Close-up view. Skin tone: Fitzpatrick skin type II.
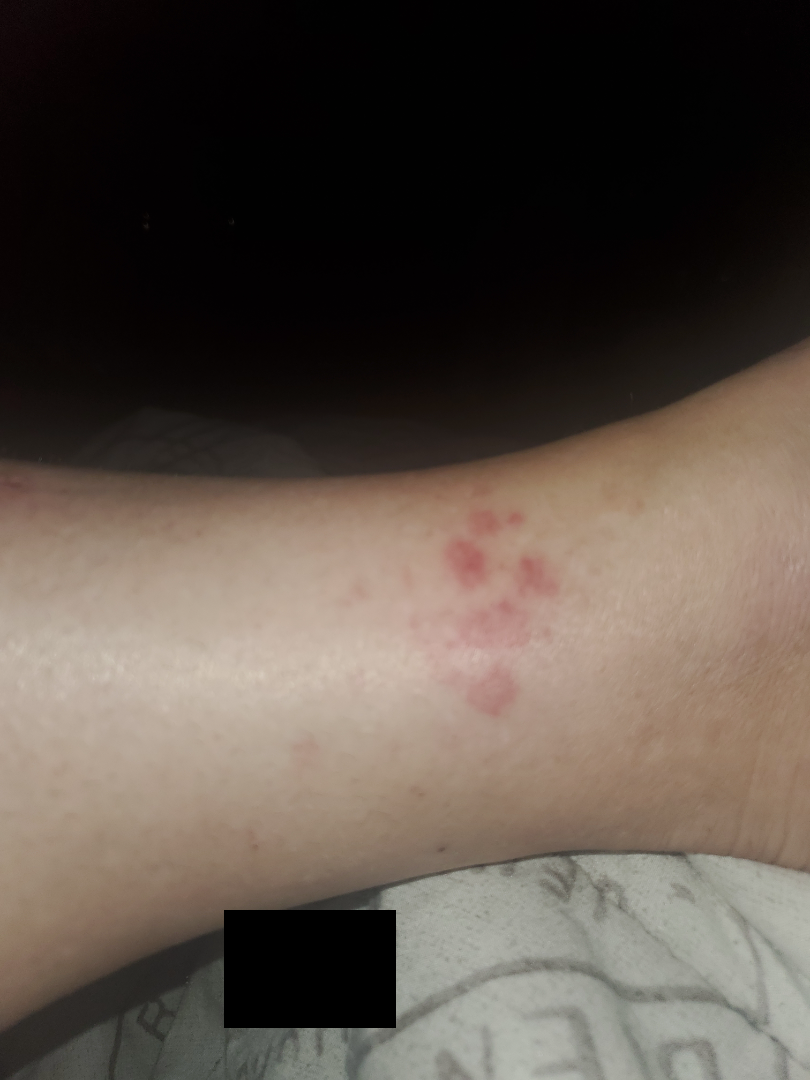Q: What conditions are considered?
A: most likely Insect Bite; also consider Allergic Contact Dermatitis; less likely is Urticaria